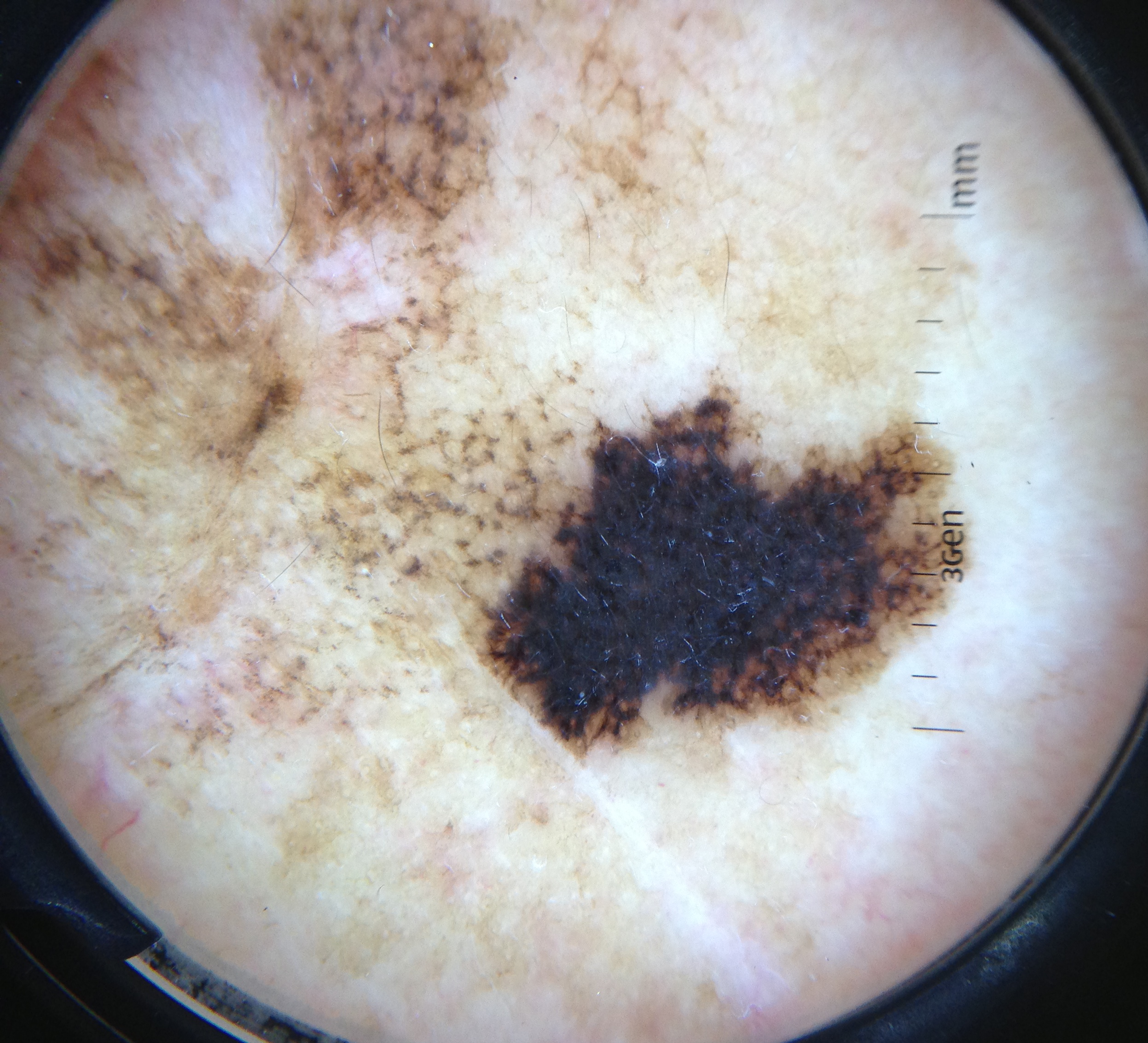diagnostic label — lentigo maligna (biopsy-proven)